Dermoscopy of a skin lesion.
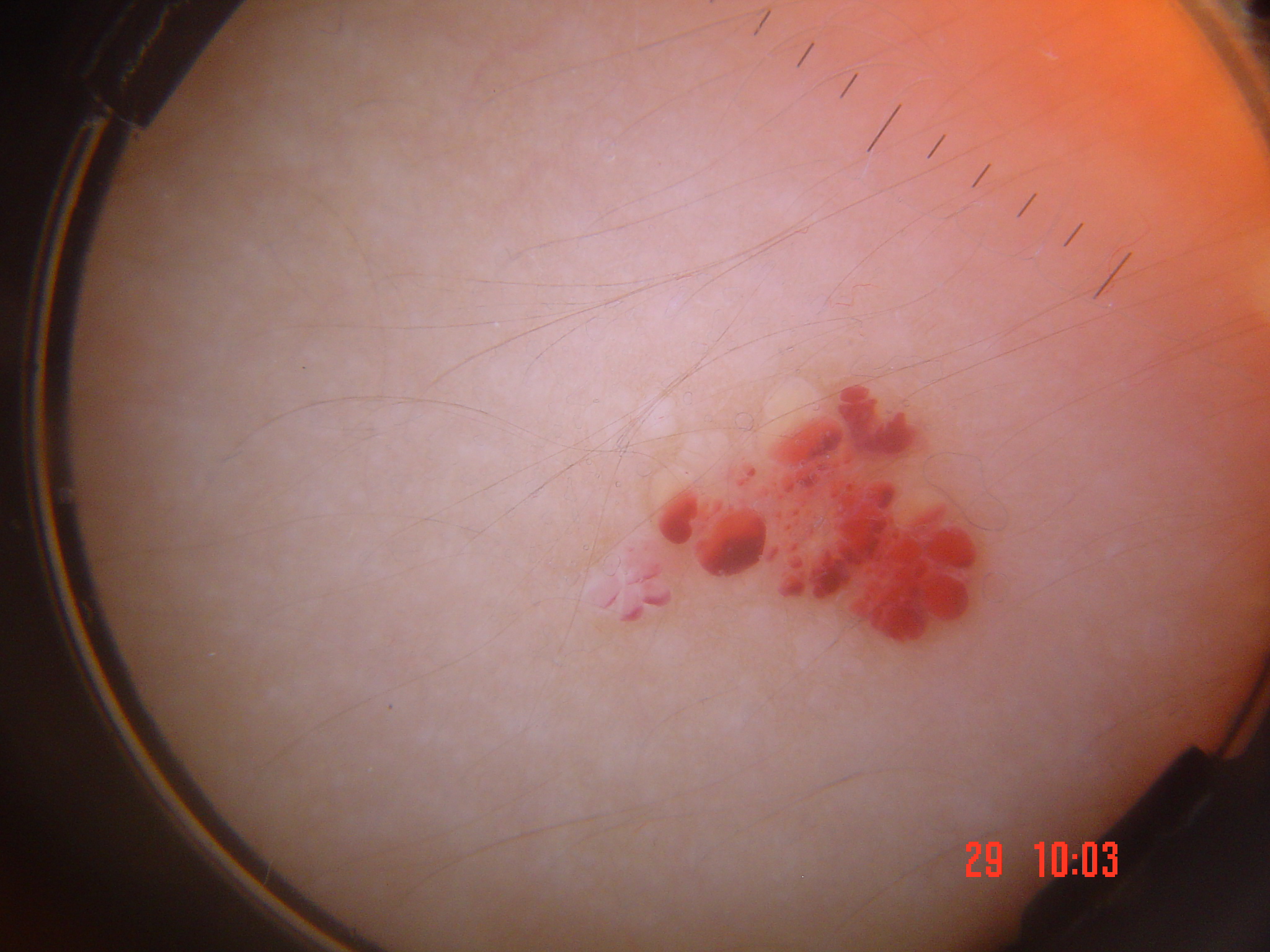– assessment: lymphangioma (expert consensus)